The photo was captured at a distance · lay reviewers estimated Monk skin tone scale 2 · the lesion is described as raised or bumpy · present for less than one week — 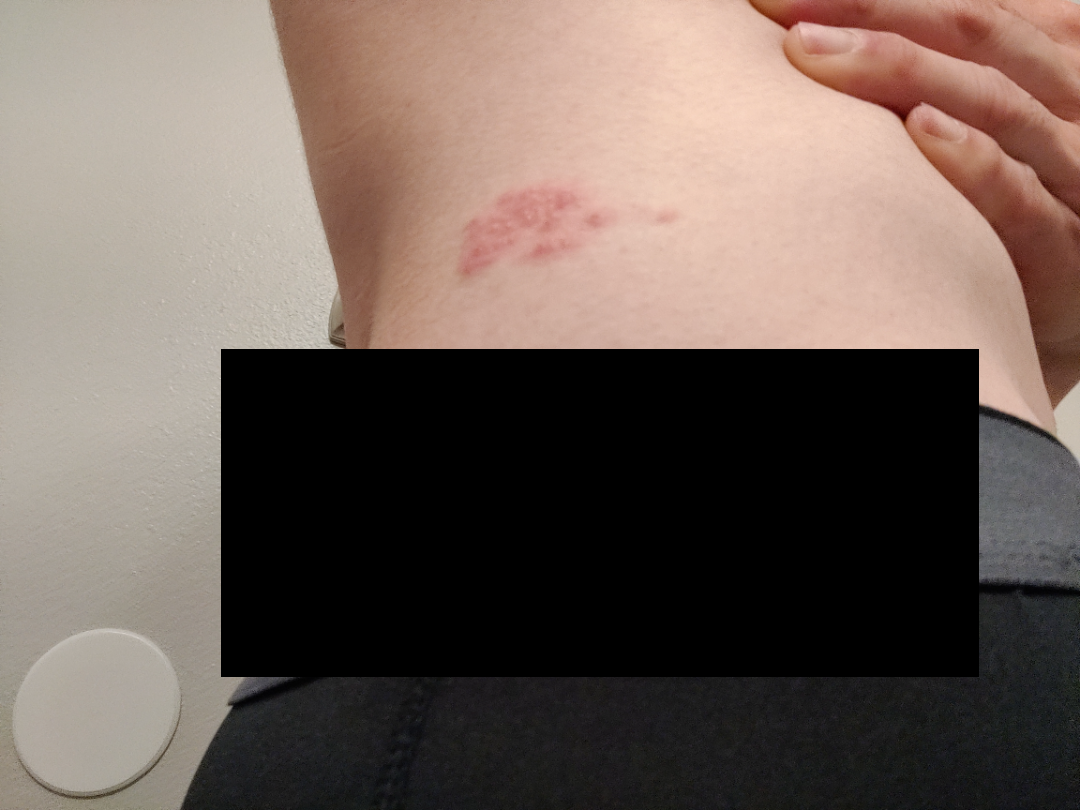On dermatologist assessment of the image, Herpes Zoster (leading).